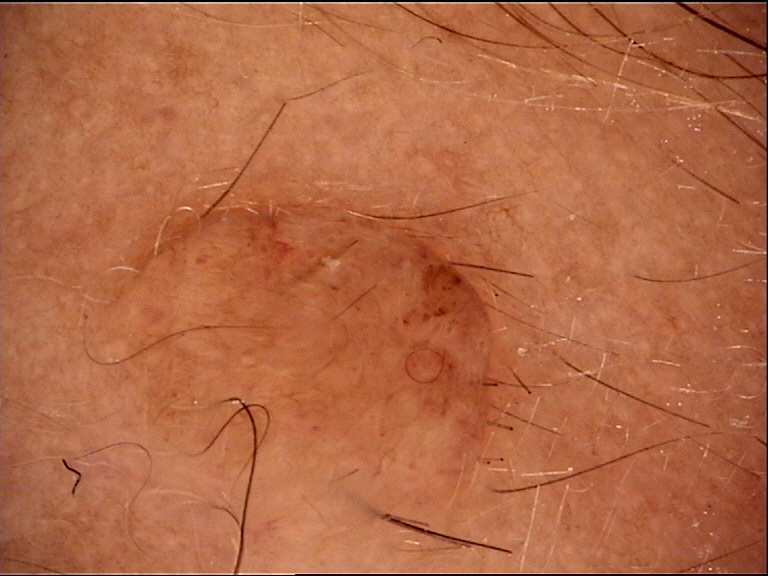A dermatoscopic image of a skin lesion. Classified as a dermal nevus.